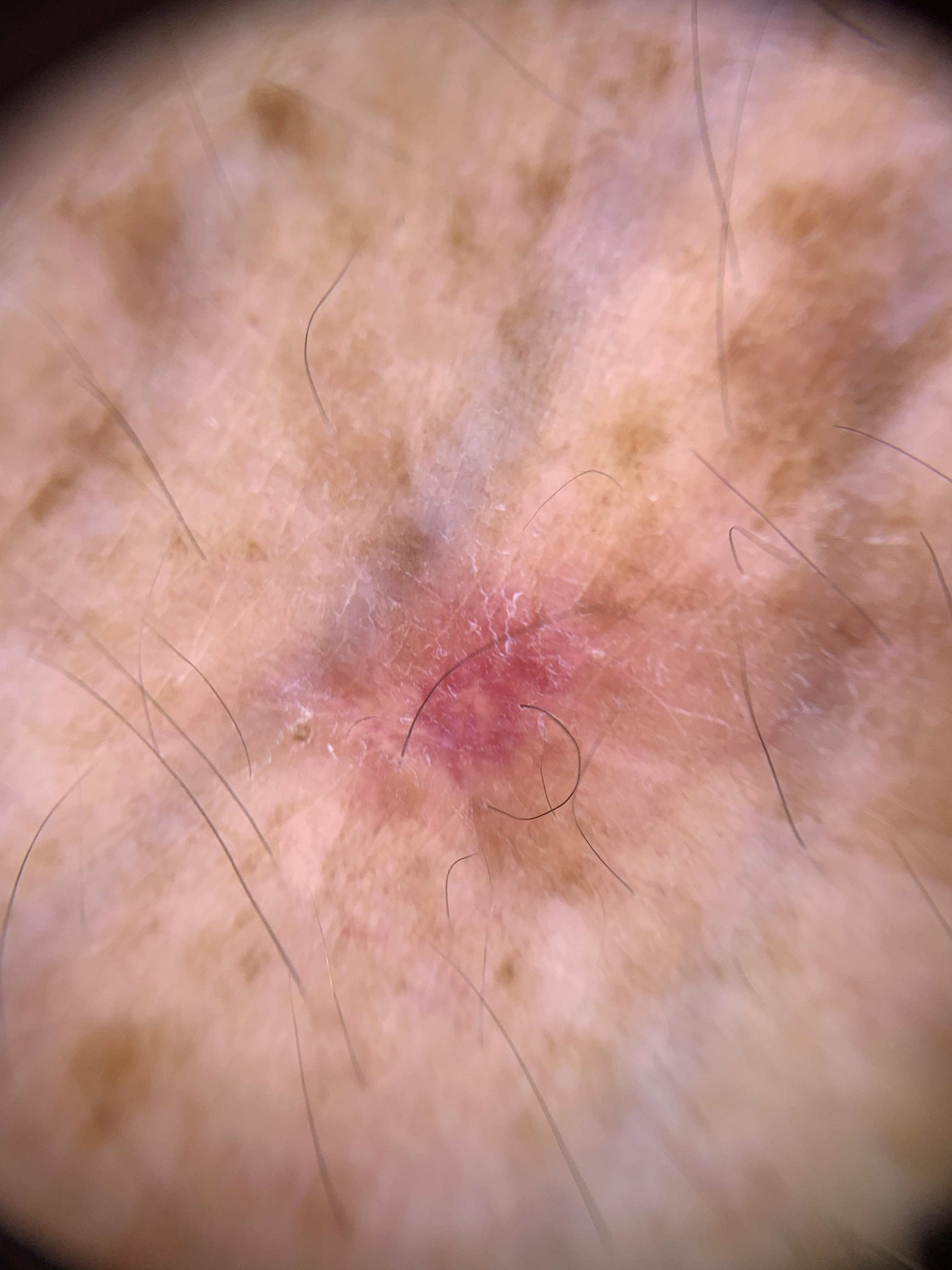A female patient aged 68-72. The patient was assessed as FST II. The chart notes no previous melanoma and no first-degree relative with melanoma. Contact-polarized dermoscopy of a skin lesion. Located on an upper extremity. Histopathological examination showed a malignant, epidermal lesion — a squamous cell carcinoma.